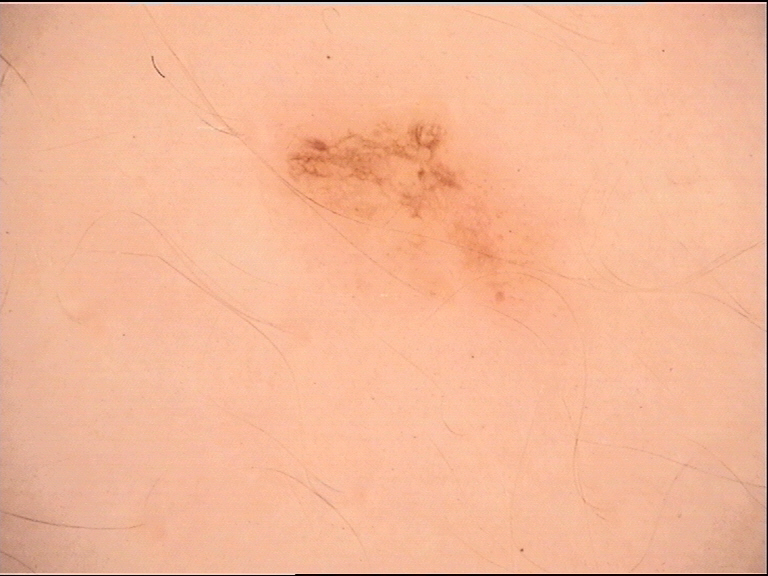label: dysplastic junctional nevus (expert consensus).